A female subject, roughly 50 years of age. A dermoscopic close-up of a skin lesion — 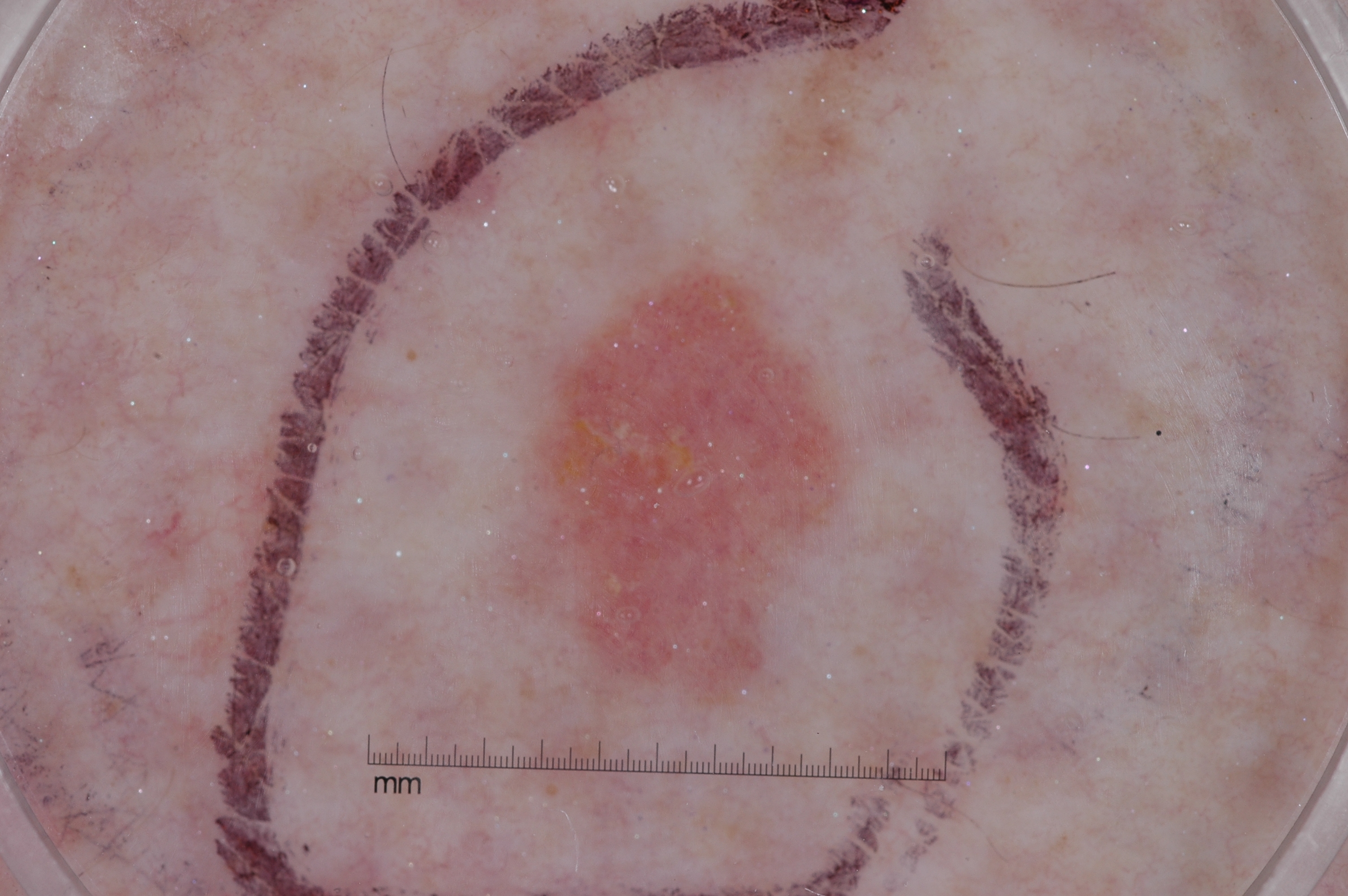Case summary:
• bounding box · <box>527, 266, 842, 693</box>
• dermoscopic features not present · milia-like cysts, streaks, negative network, and pigment network
• diagnosis · a seborrheic keratosis, a non-melanocytic (keratinocytic) lesion